The lesion involves the arm and back of the hand, close-up view, the patient is a male aged 18–29.
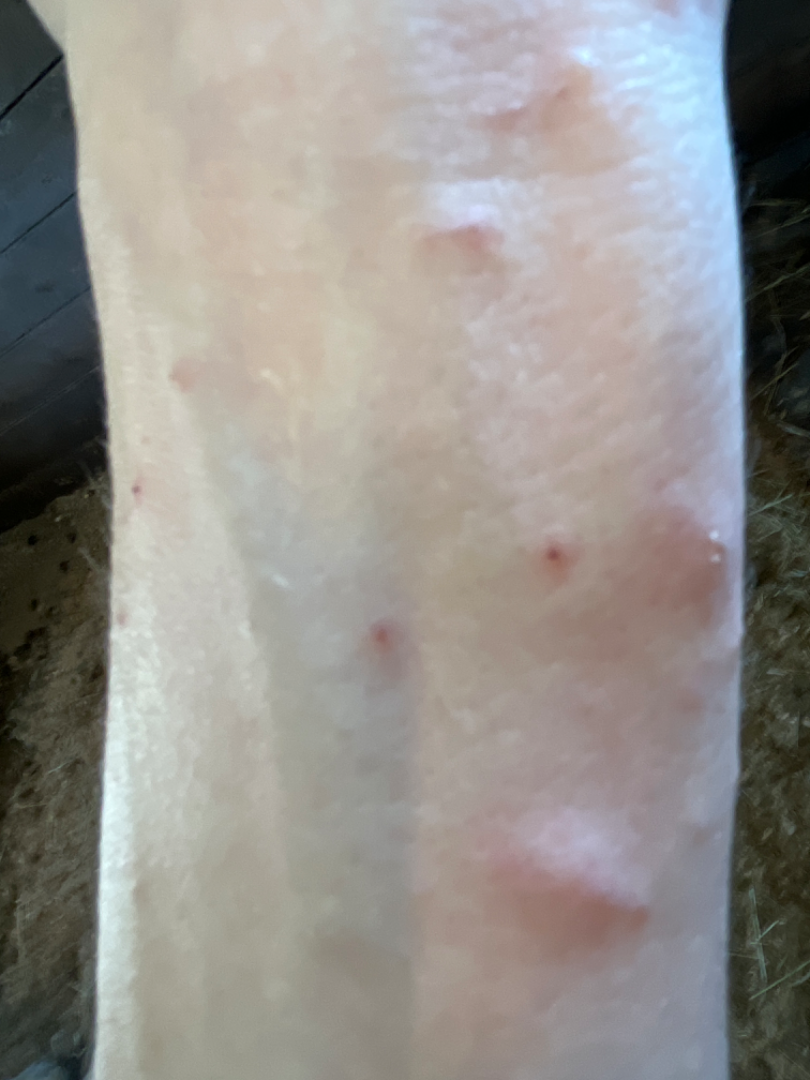* assessment — indeterminate from the photograph
* patient describes the issue as — a rash
* lesion texture — raised or bumpy
* reported symptoms — itching and bothersome appearance
* onset — one to four weeks